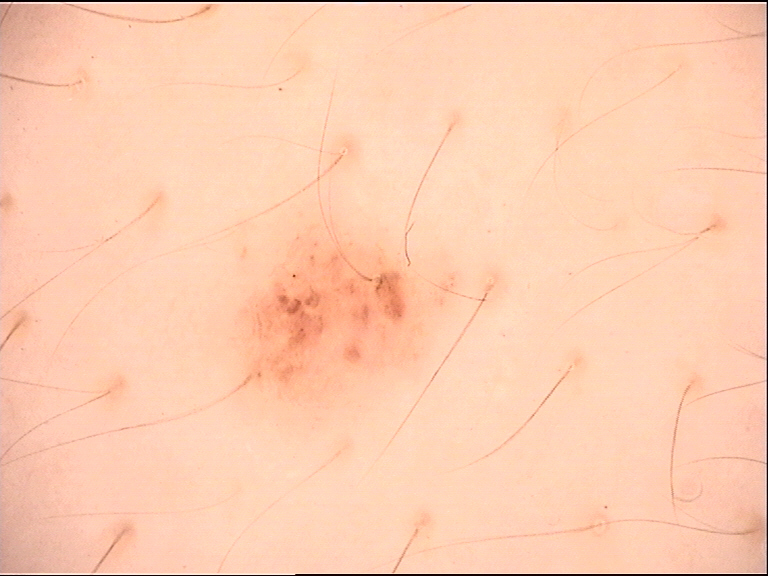Impression:
The diagnostic label was a banal lesion — a compound nevus.